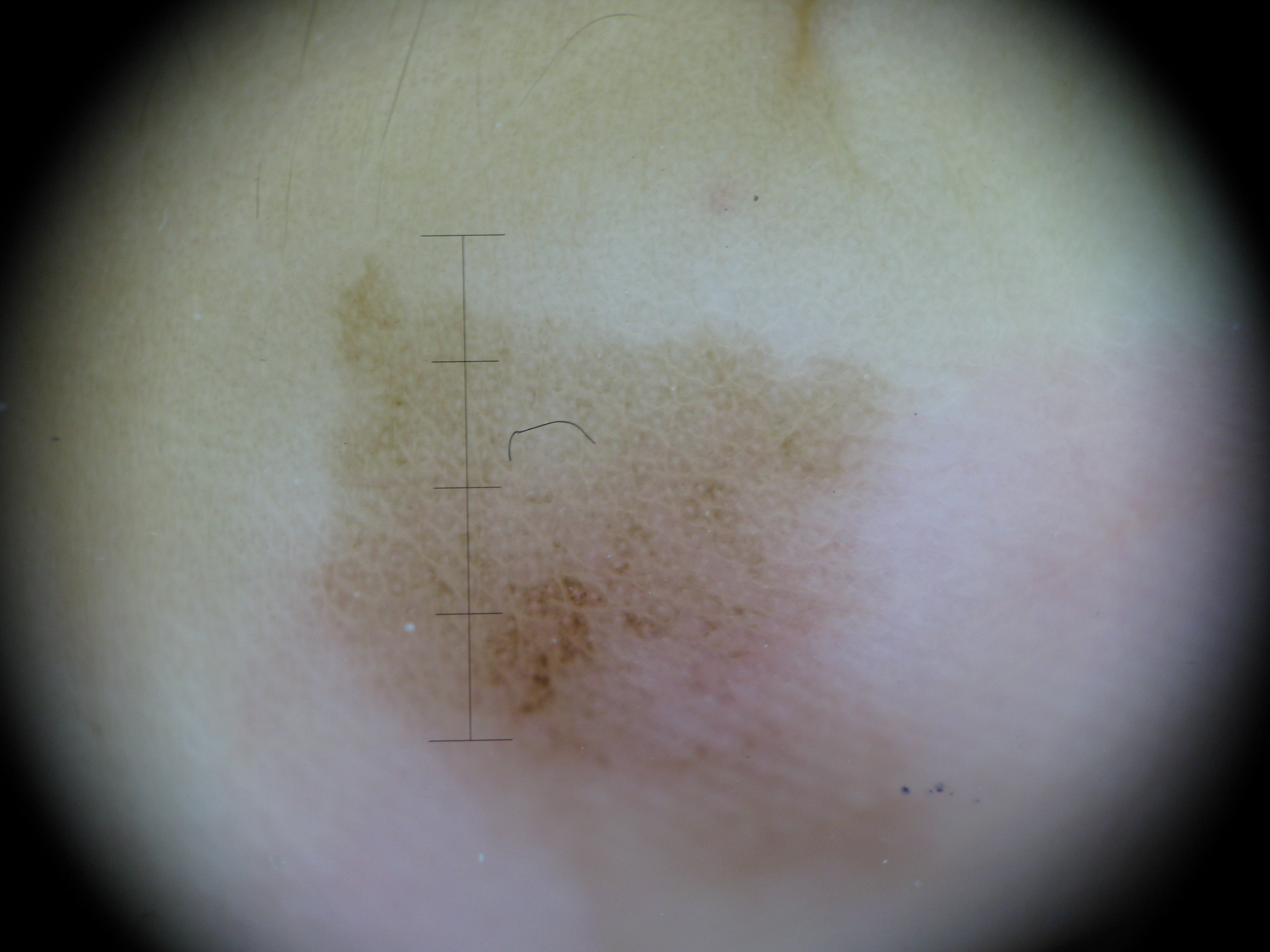This is a banal lesion.
The diagnostic label was an acral junctional nevus.